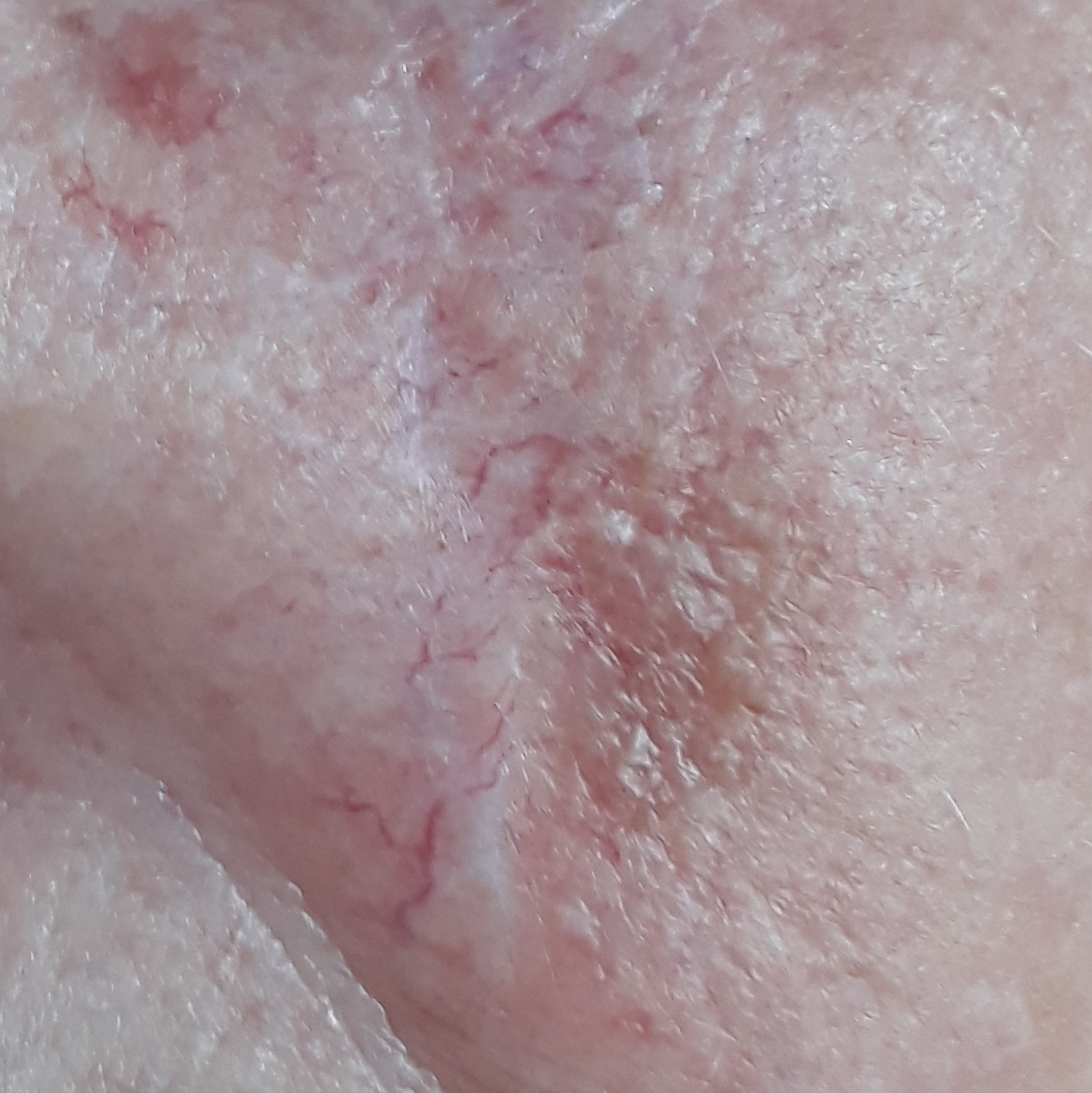skin type — III | modality — clinical photograph | exposure history — pesticide exposure, prior malignancy (patient or family), no prior skin cancer (patient or family), no tobacco use | subject — female, in their mid-50s | region — the face | size — 15x10 mm | symptoms — elevation / no itching | diagnostic label — basal cell carcinoma (biopsy-proven).